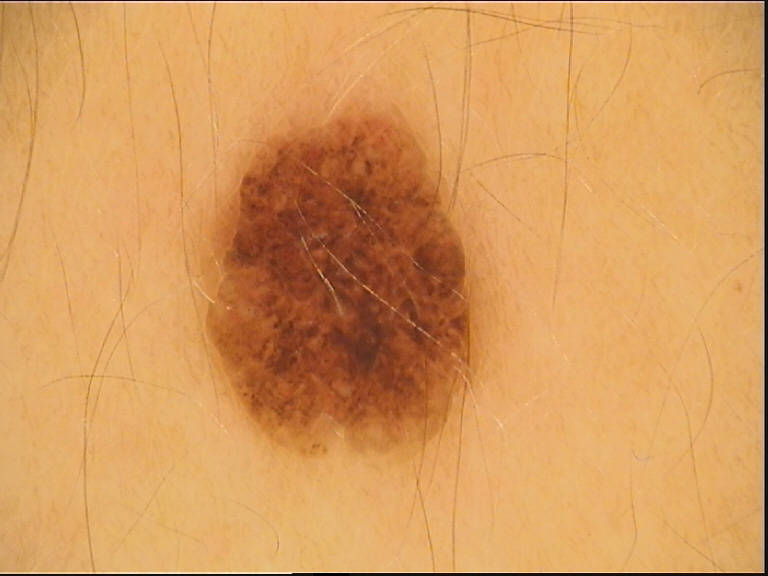modality: dermoscopy | subtype: banal | diagnosis: compound nevus (expert consensus).